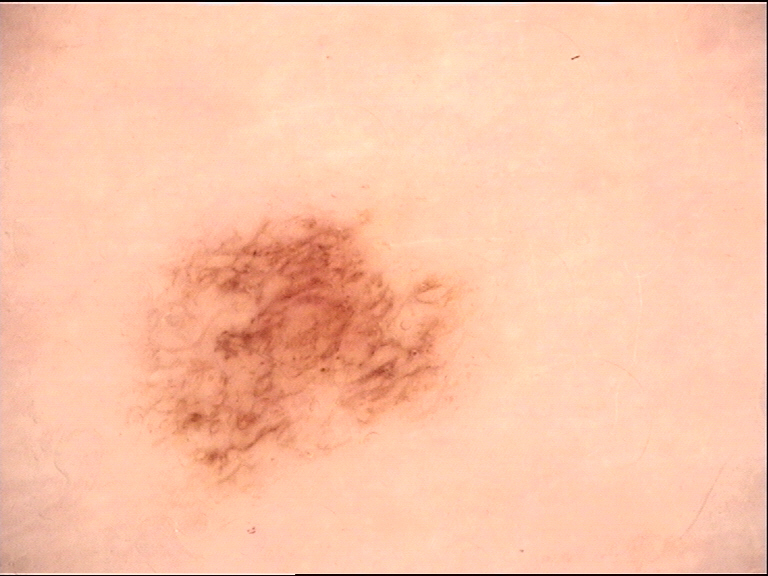Impression:
Labeled as a benign lesion — a dysplastic junctional nevus.